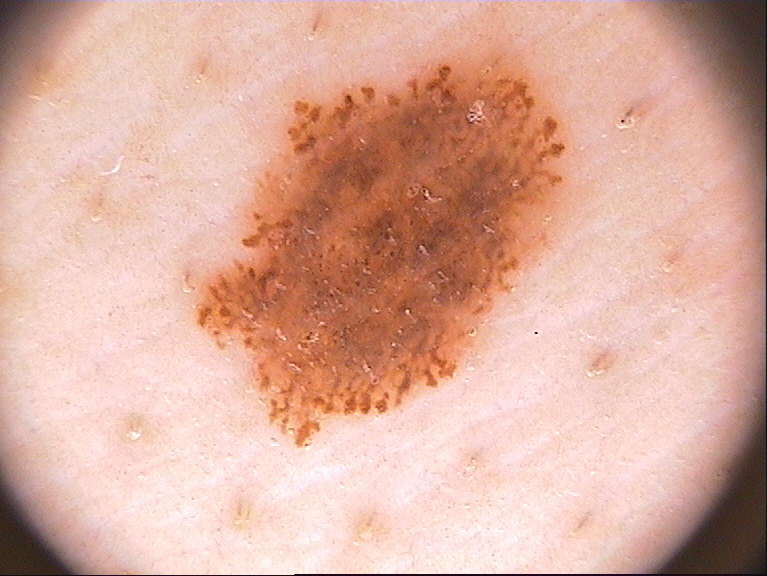{
  "image": {
    "modality": "dermoscopy"
  },
  "patient": {
    "sex": "male"
  },
  "dermoscopic_features": {
    "present": [
      "globules",
      "streaks",
      "pigment network"
    ],
    "absent": [
      "milia-like cysts",
      "negative network"
    ]
  },
  "lesion_location": {
    "bbox_xyxy": [
      194,
      43,
      580,
      449
    ]
  },
  "diagnosis": {
    "name": "melanocytic nevus",
    "malignancy": "benign",
    "lineage": "melanocytic",
    "provenance": "clinical"
  }
}